Dermoscopy of a skin lesion.
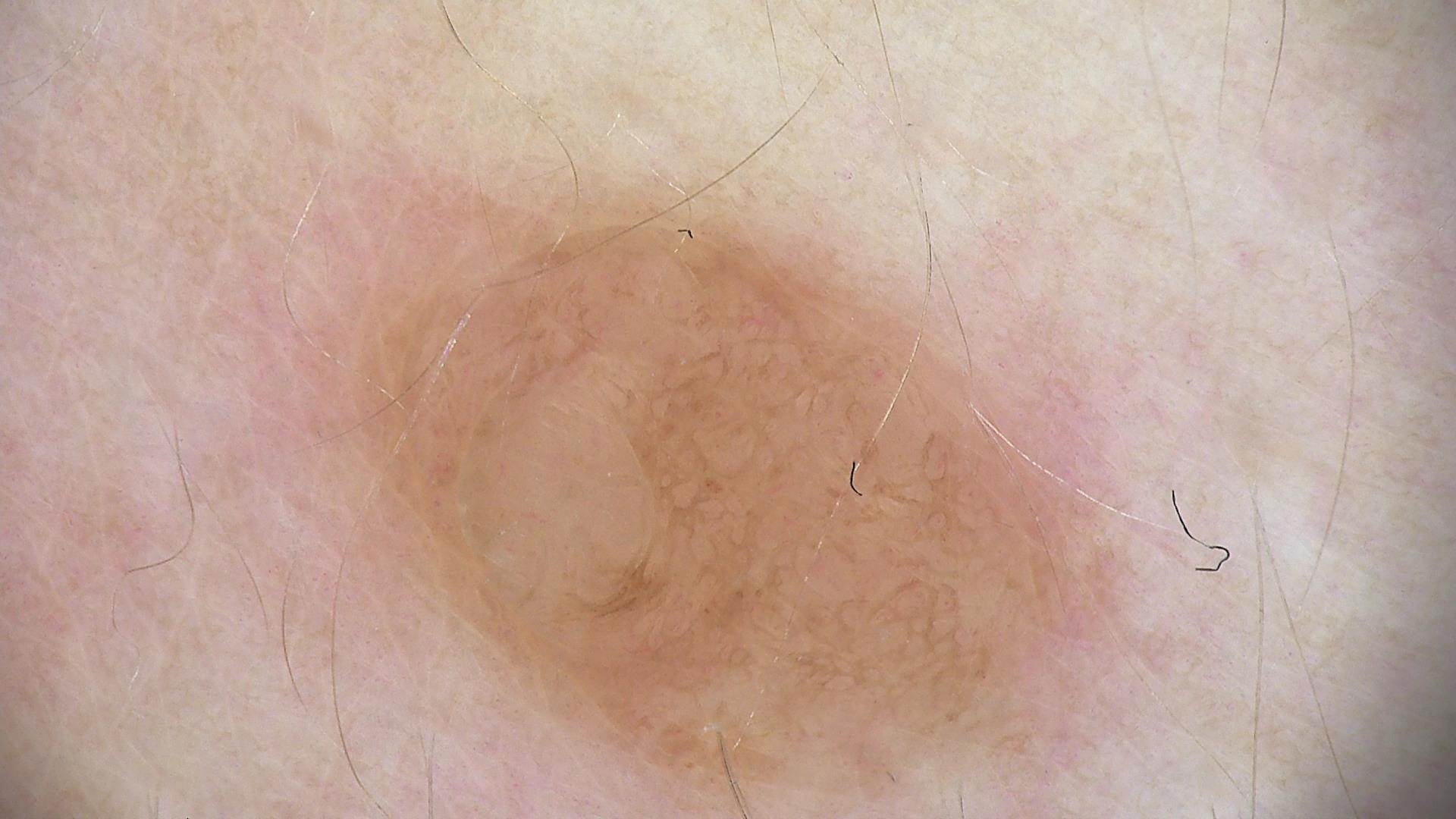Findings:
The morphology is that of a banal lesion.
Conclusion:
The diagnostic label was a dermal nevus.